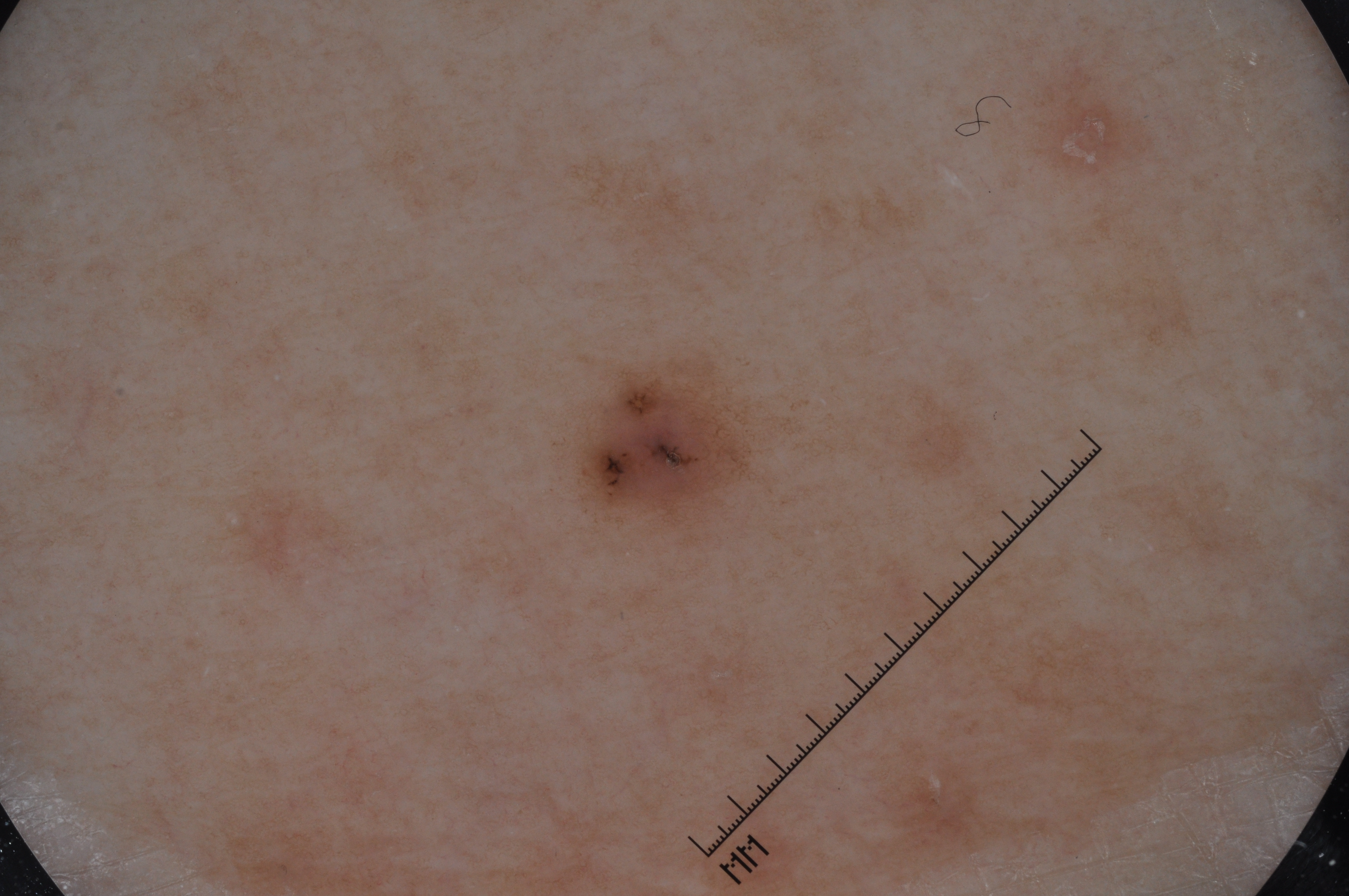| feature | finding |
|---|---|
| modality | dermoscopic image |
| bounding box | [569,365,759,525] |
| diagnosis | a melanocytic nevus |